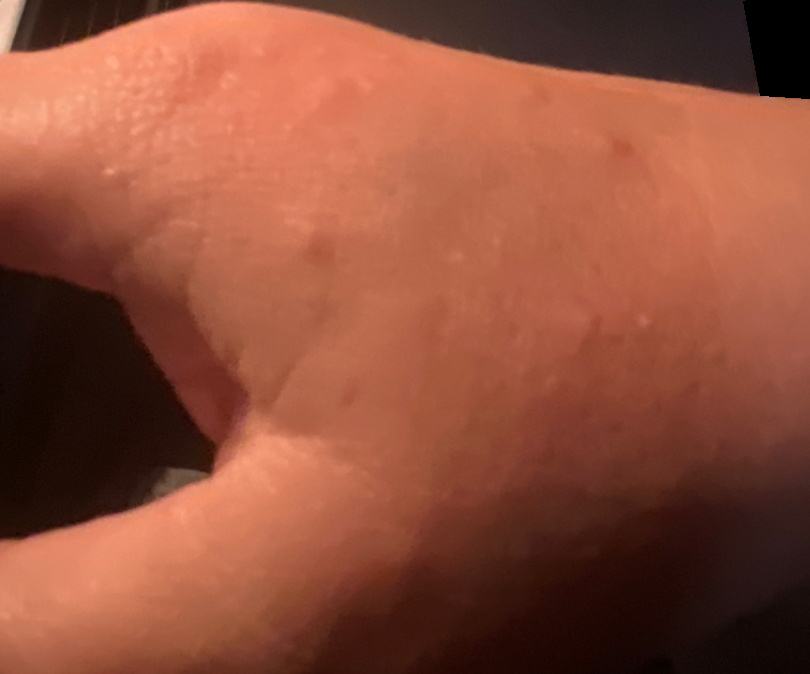The case was difficult to assess from the available photograph.
The patient described the issue as skin that appeared healthy to them.
The affected area is the back of the hand.
An image taken at an angle.
The condition has been present for one to four weeks.
Fitzpatrick skin type III; non-clinician graders estimated MST 2.
Texture is reported as raised or bumpy.